A wide-field clinical photograph of a skin lesion · a male patient aged 68-72: 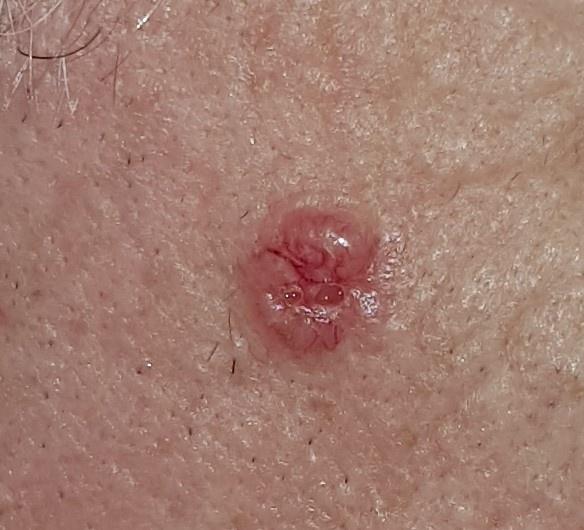<skin_lesion>
  <lesion_location>
    <region>the head or neck</region>
  </lesion_location>
  <diagnosis>
    <name>Basal cell carcinoma</name>
    <malignancy>malignant</malignancy>
    <confirmation>histopathology</confirmation>
    <lineage>adnexal</lineage>
  </diagnosis>
</skin_lesion>